A dermoscopic image of a skin lesion: 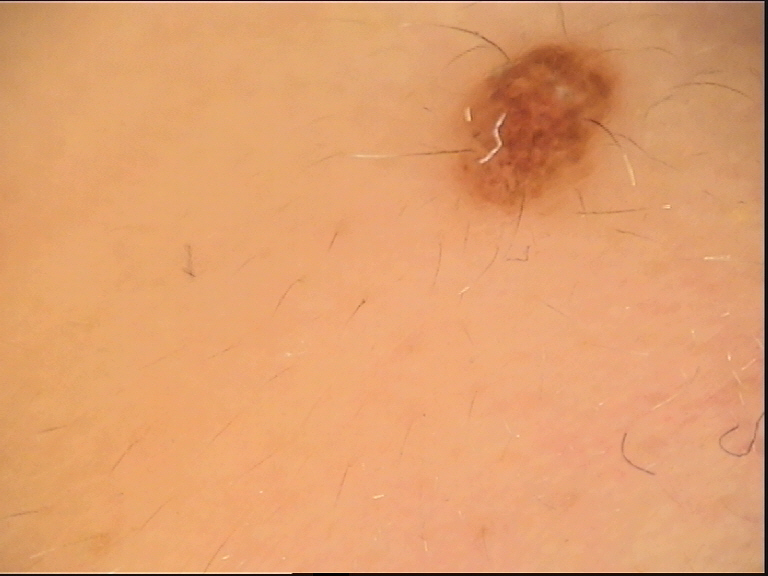{
  "diagnosis": {
    "name": "dysplastic compound nevus",
    "code": "cd",
    "malignancy": "benign",
    "super_class": "melanocytic",
    "confirmation": "expert consensus"
  }
}